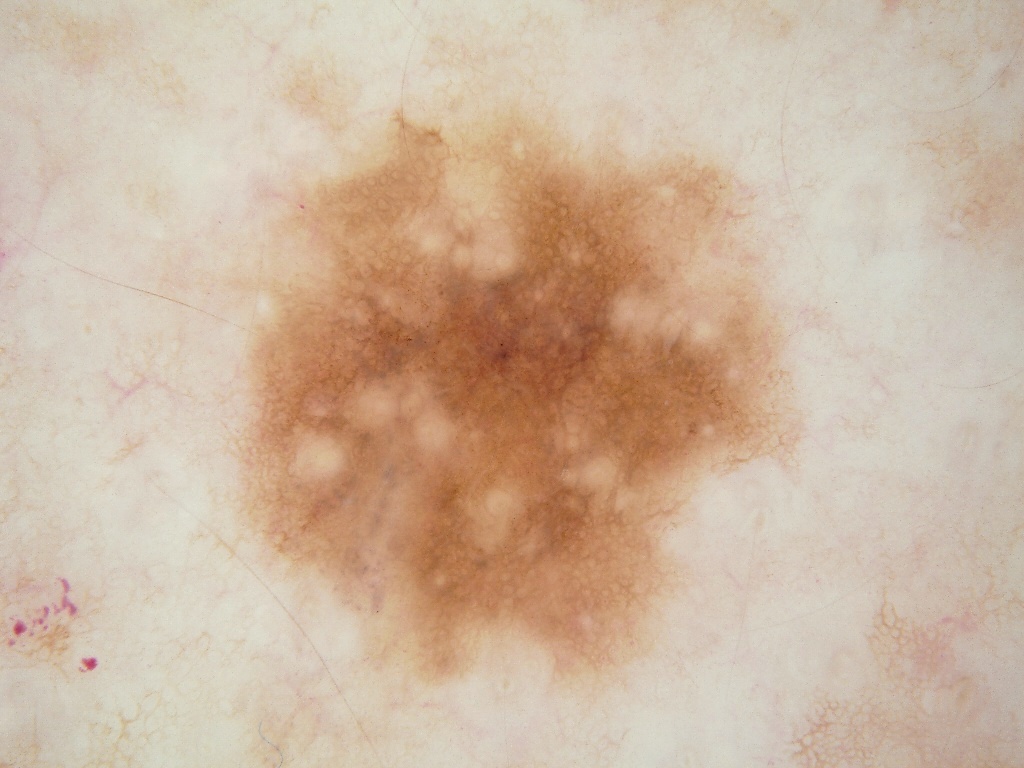Case summary:
A female patient, in their mid- to late 40s. A dermoscopy image of a single skin lesion. A large lesion occupying much of the field. Dermoscopically, the lesion shows pigment network and milia-like cysts. In (x1, y1, x2, y2) order, lesion location: bbox=[222, 86, 798, 707].
Impression:
Expert review diagnosed this as a melanocytic nevus, a benign skin lesion.